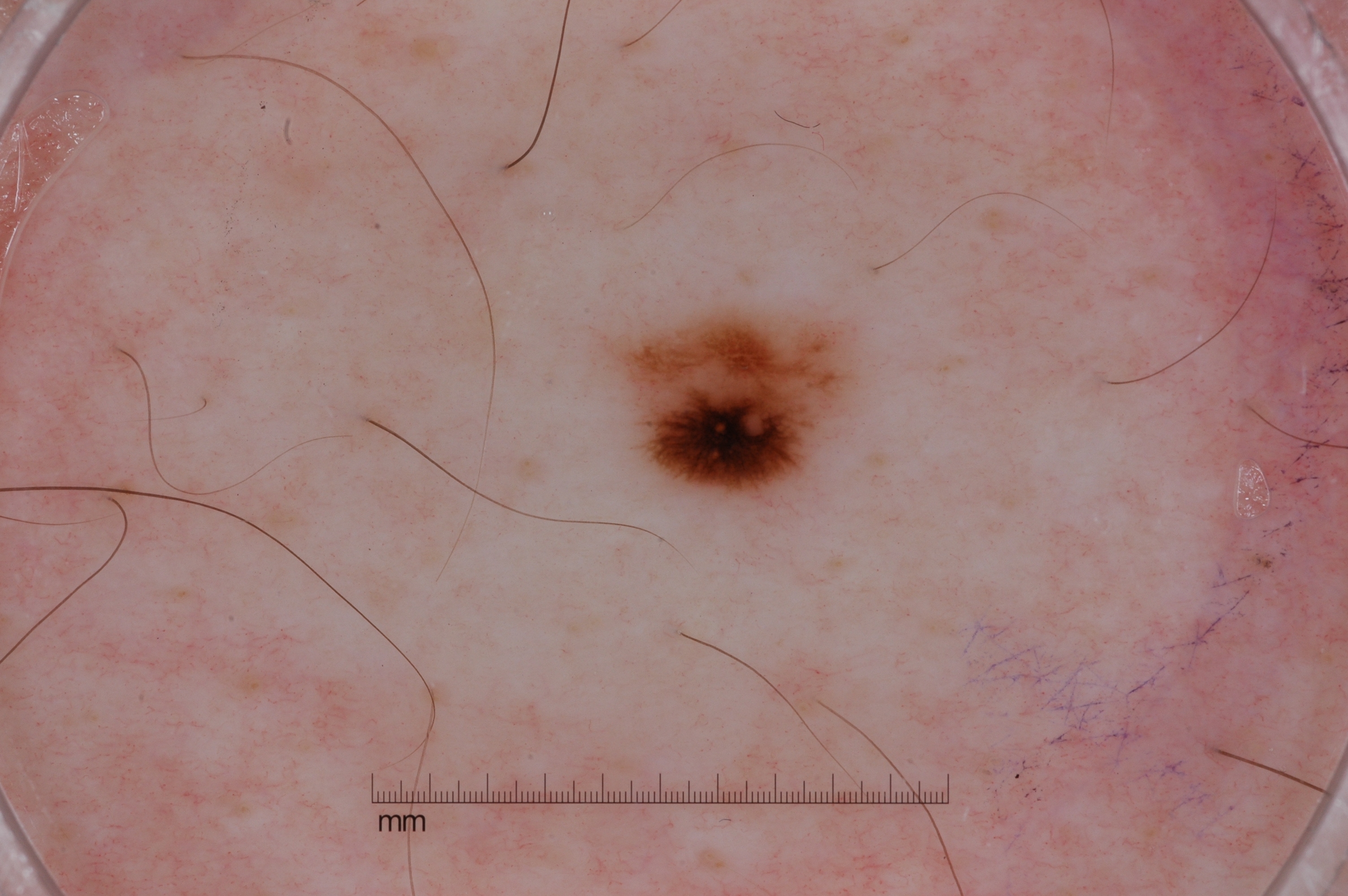modality = dermoscopy of a skin lesion
bounding box = x1=611 y1=308 x2=853 y2=504
dermoscopic features = negative network and pigment network; absent: streaks and milia-like cysts
impression = a melanoma, a skin cancer